A female patient aged 92. The patient says their skin tans without first burning — 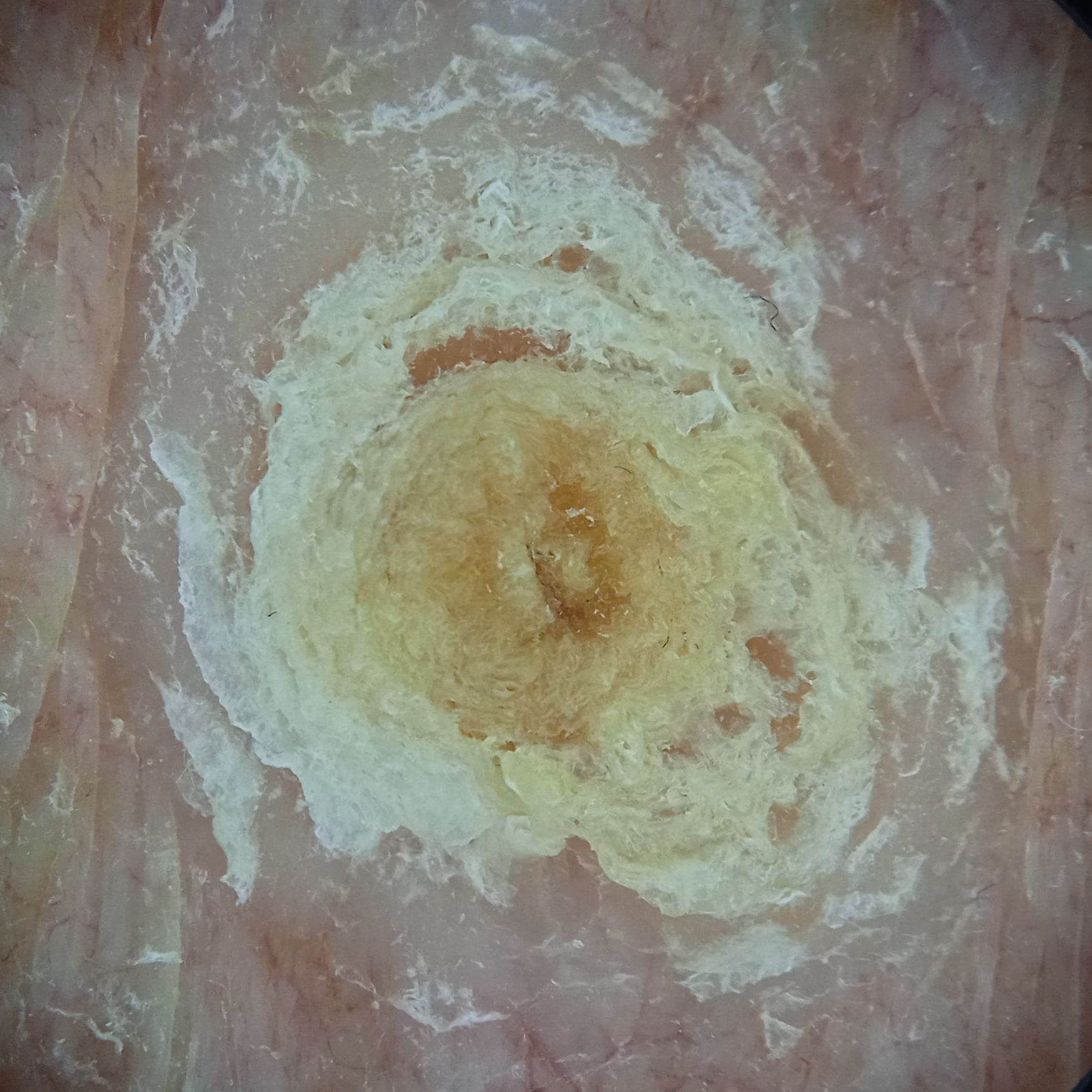Findings: The lesion involves the torso. Conclusion: The dermatologists' assessment was a squamous cell carcinoma.